The photograph is a close-up of the affected area — 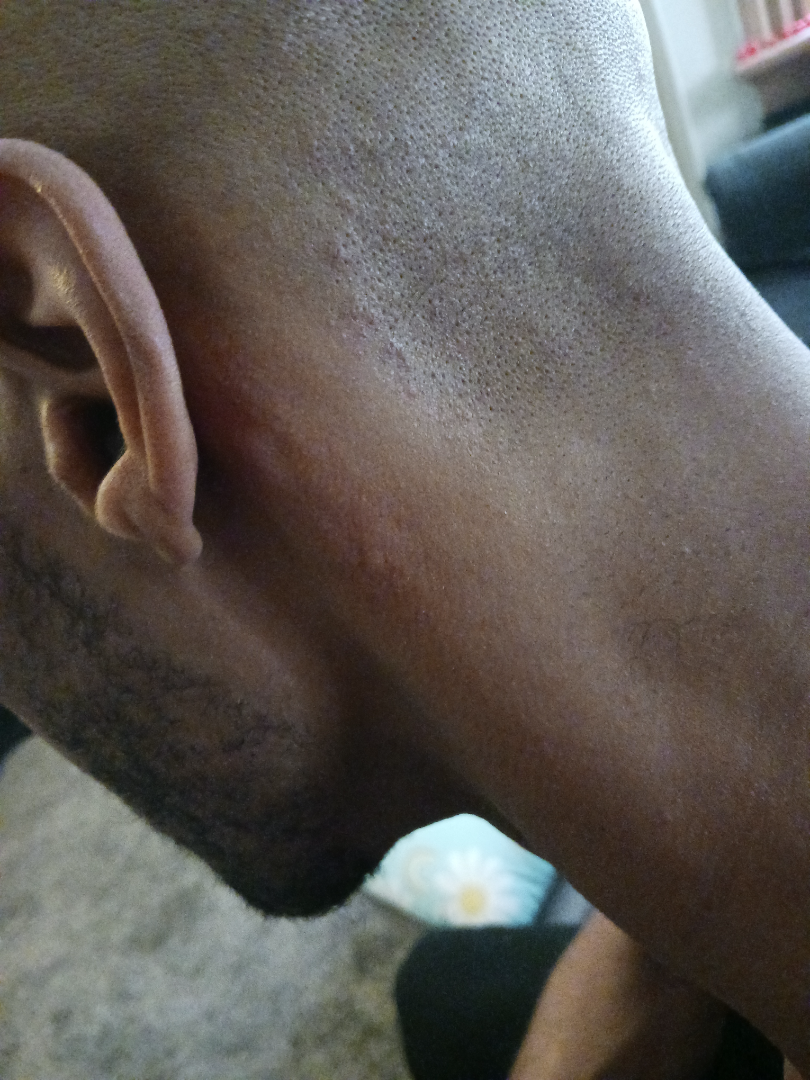The case was difficult to assess from the available photograph.